A dermoscopic view of a skin lesion: 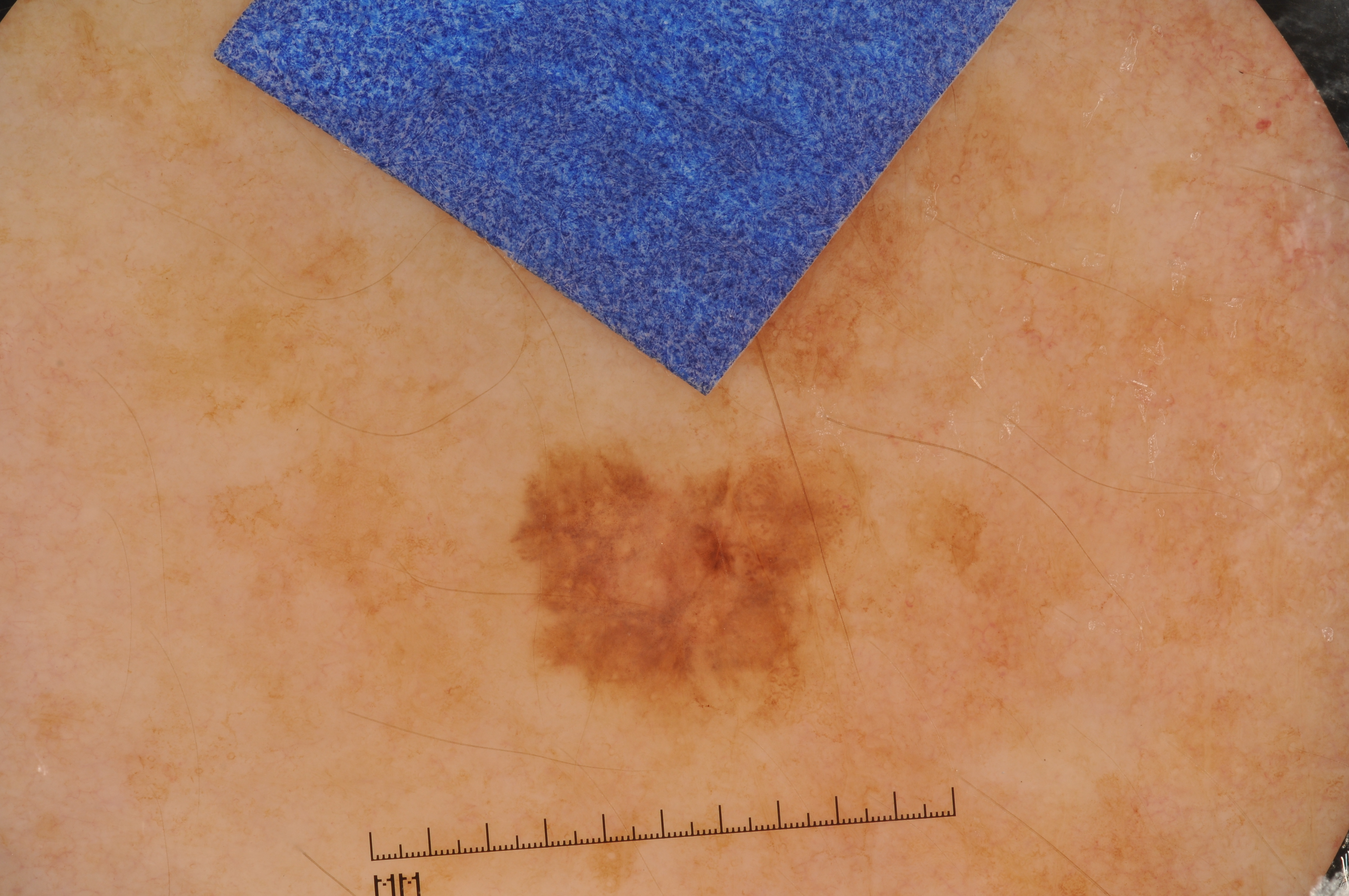• bounding box — (517, 449, 854, 714)
• diagnostic label — a melanoma